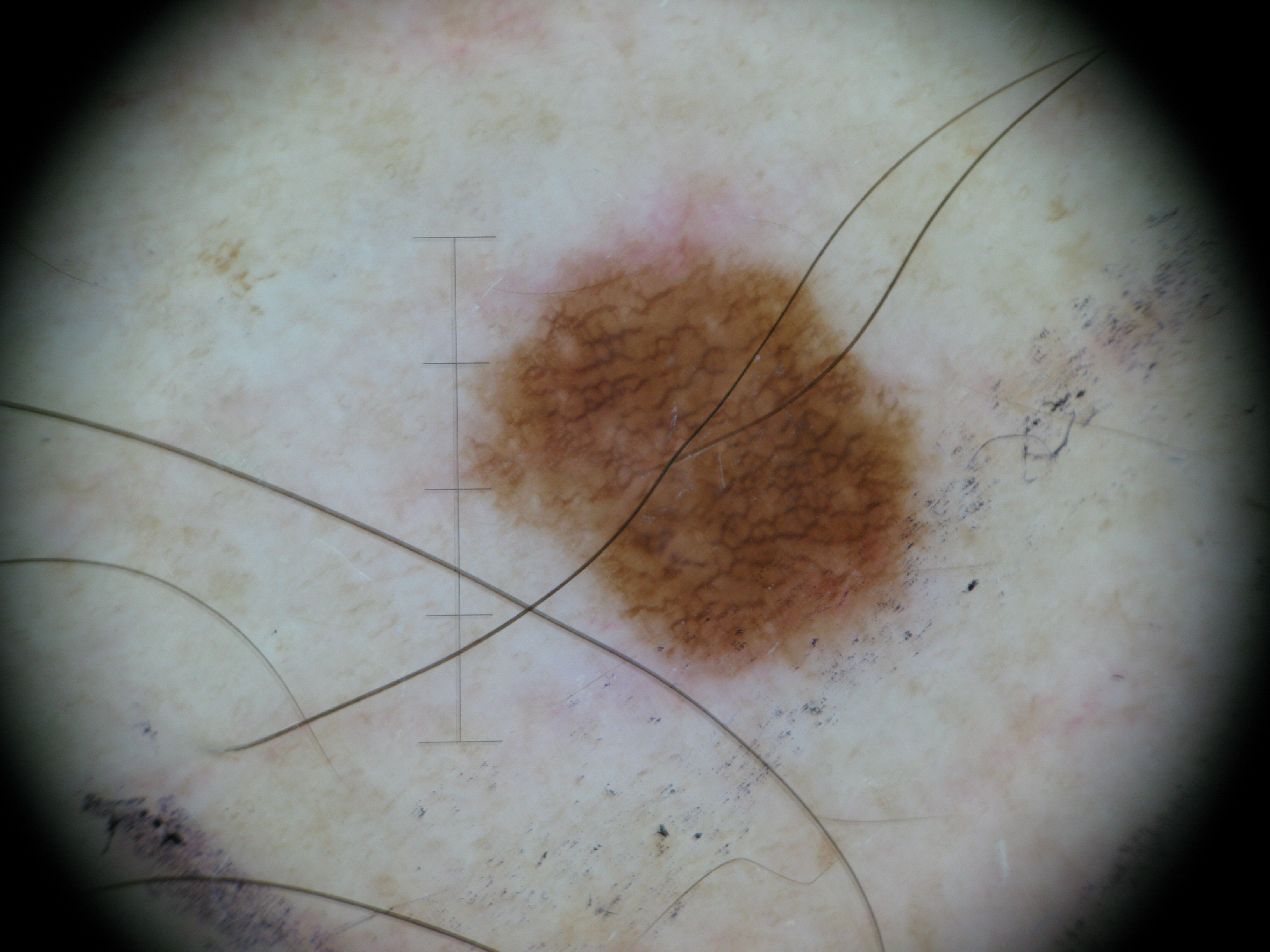Dermoscopy of a skin lesion. The architecture is that of a banal lesion. Diagnosed as a junctional nevus.